A female patient 37 years of age · the chart records prior malignancy (patient or family) and alcohol use · FST IV · a clinical photograph of a skin lesion.
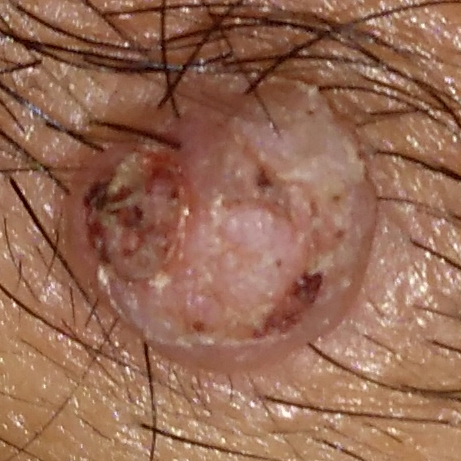Patient and lesion:
The lesion is located on the face.
Pathology:
Biopsy-confirmed as a lesion of indeterminate malignant potential — an actinic keratosis.